A dermoscopic image of a skin lesion: 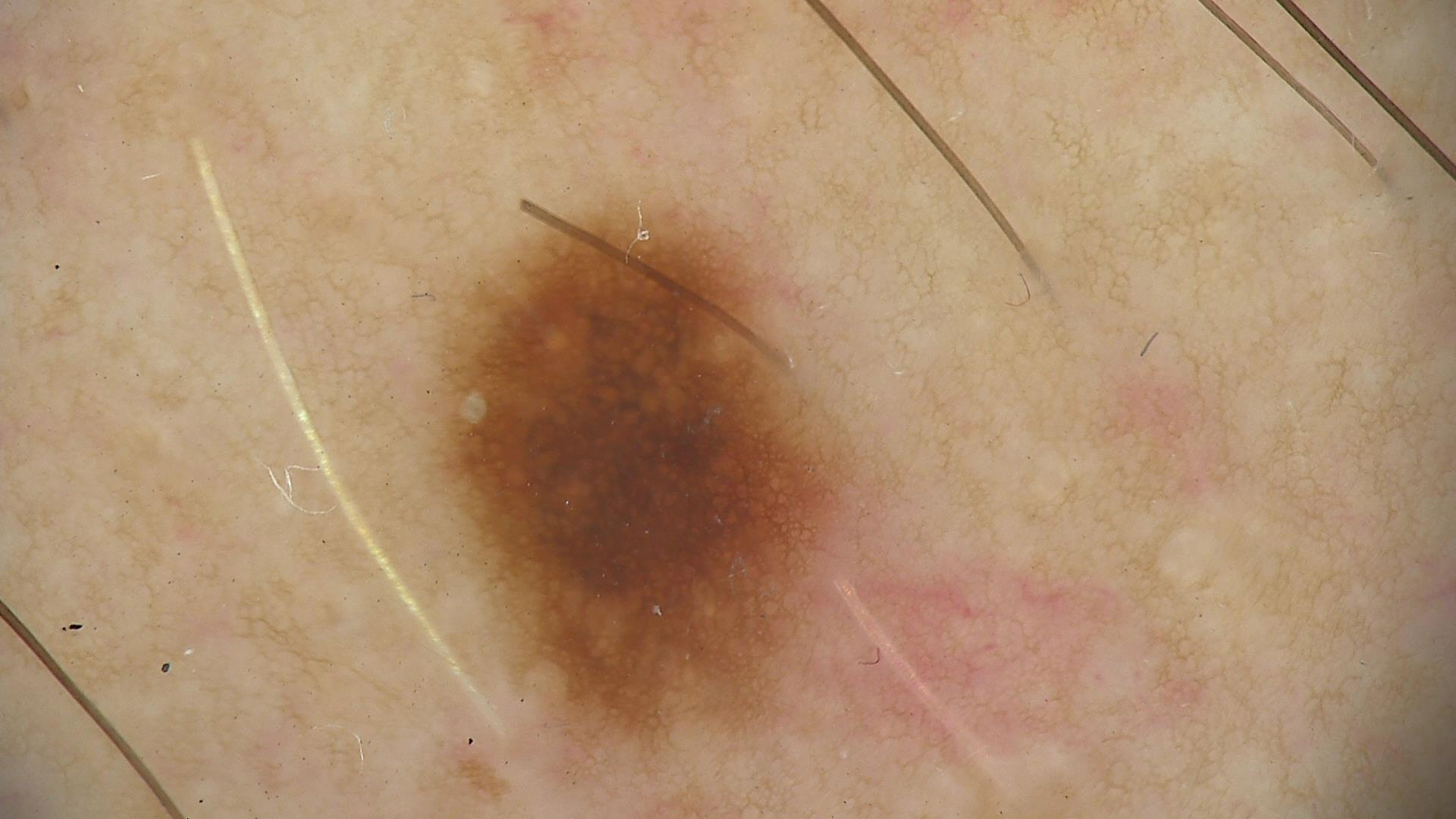label = dysplastic junctional nevus (expert consensus).